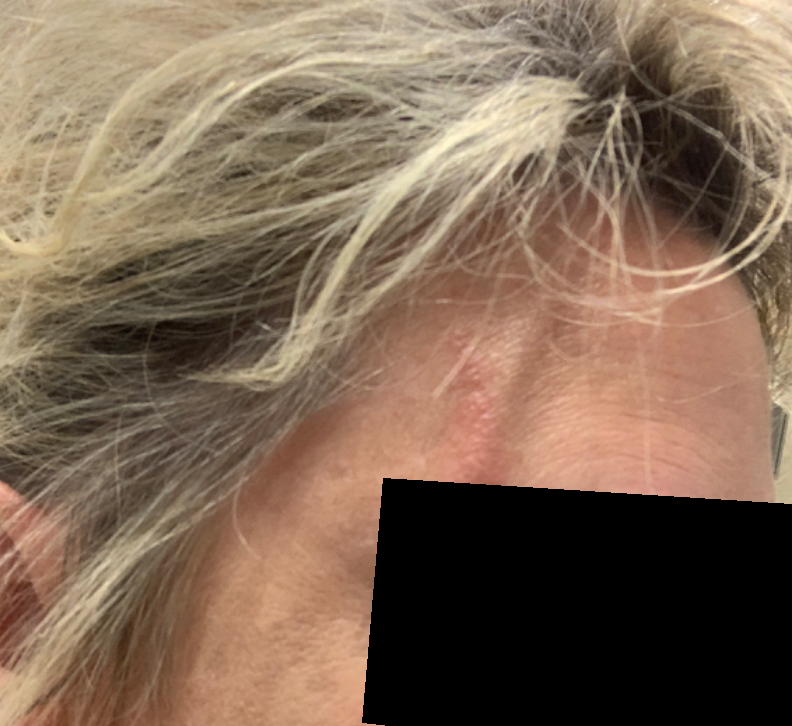Impression:
The case was difficult to assess from the available photograph.